A dermoscopic image of a skin lesion.
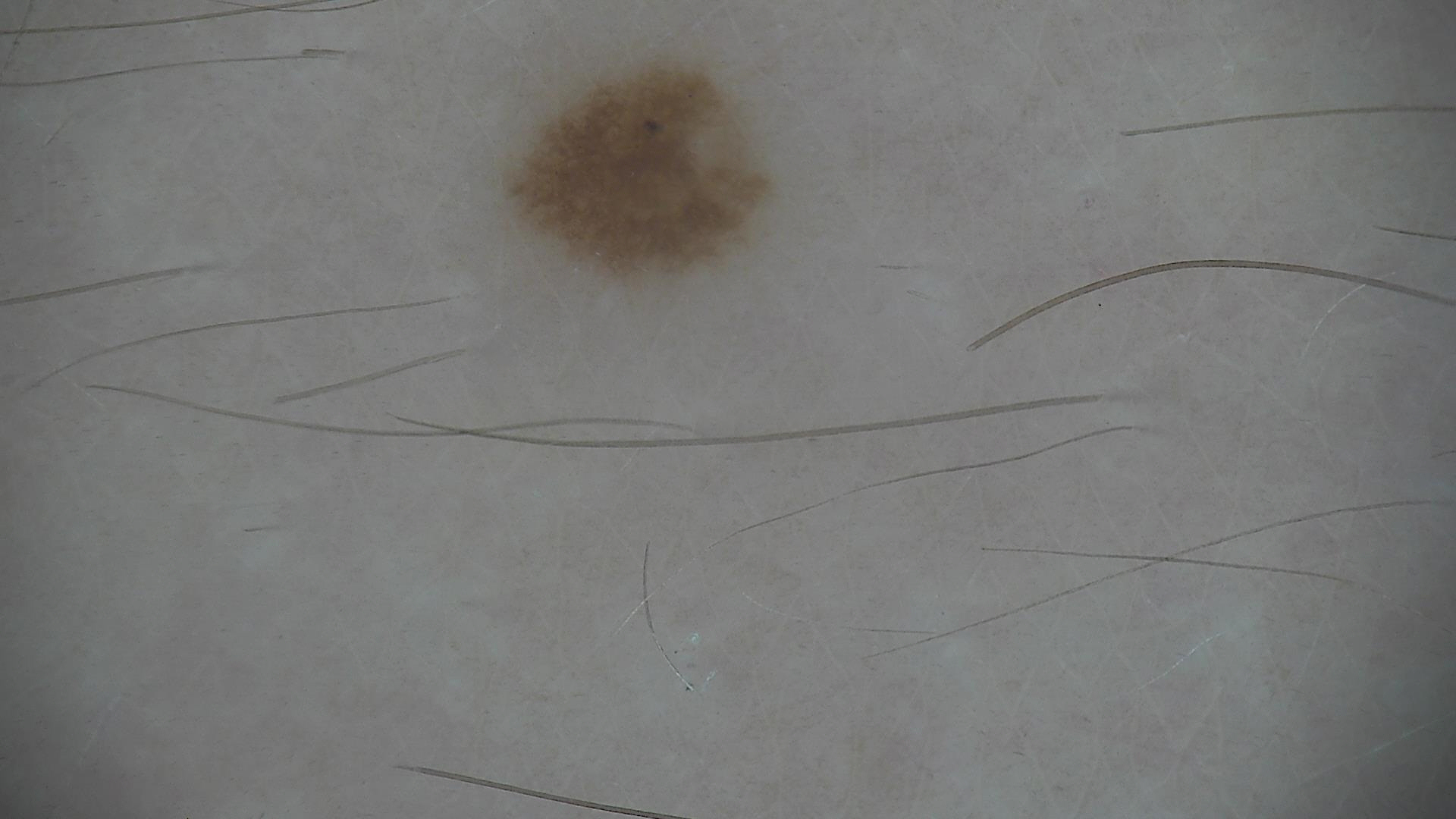Classified as a dysplastic junctional nevus.